A dermoscopic photograph of a skin lesion.
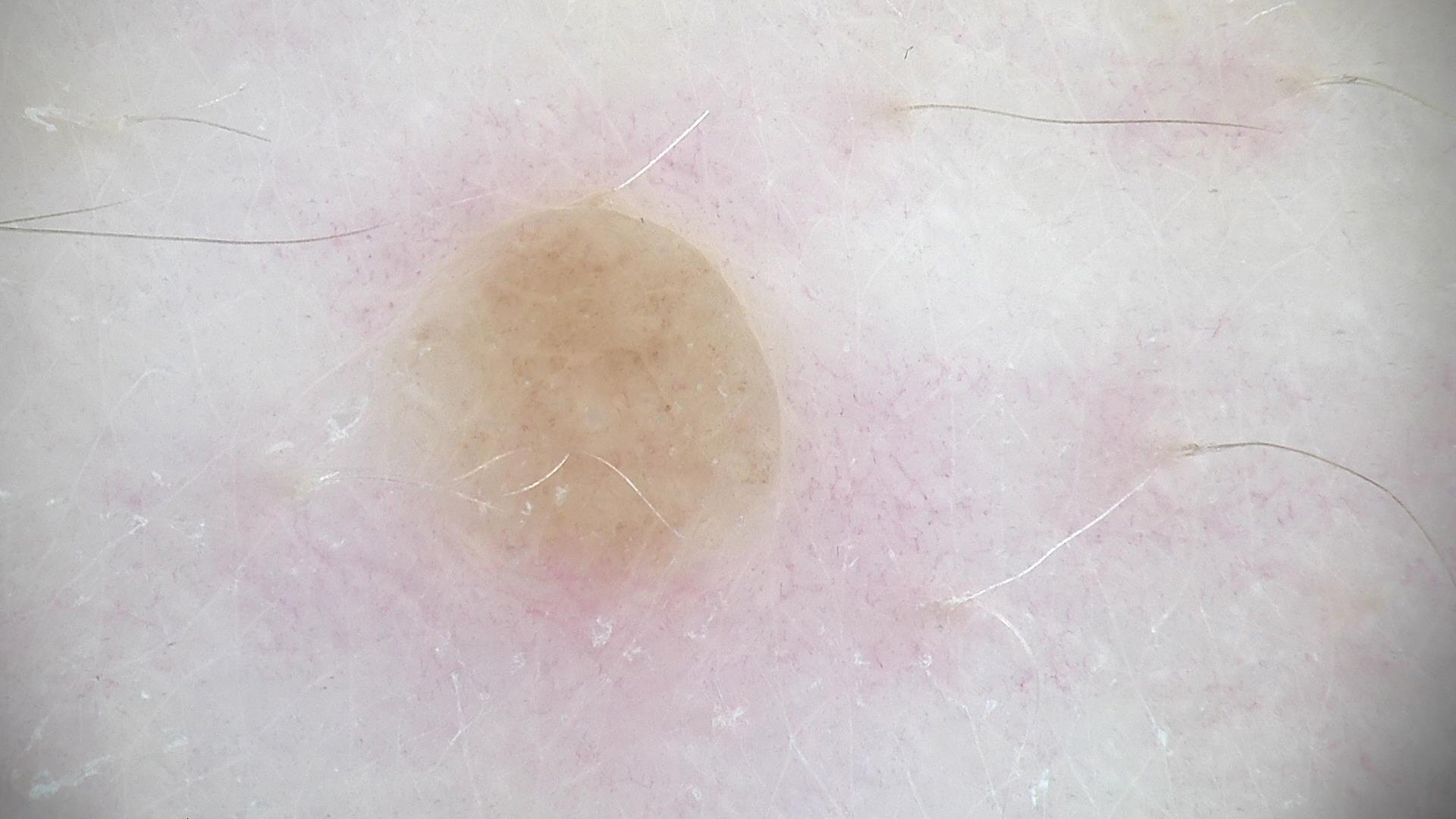The diagnostic label was a banal lesion — a dermal nevus.